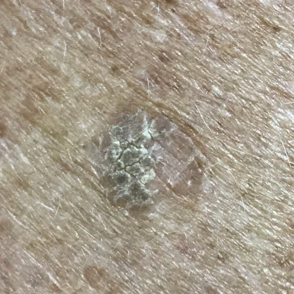A clinical photograph of a skin lesion.
The lesion was found on an arm.
The patient reports that the lesion is elevated, has grown, and itches.
The consensus clinical diagnosis was a benign skin lesion — a seborrheic keratosis.